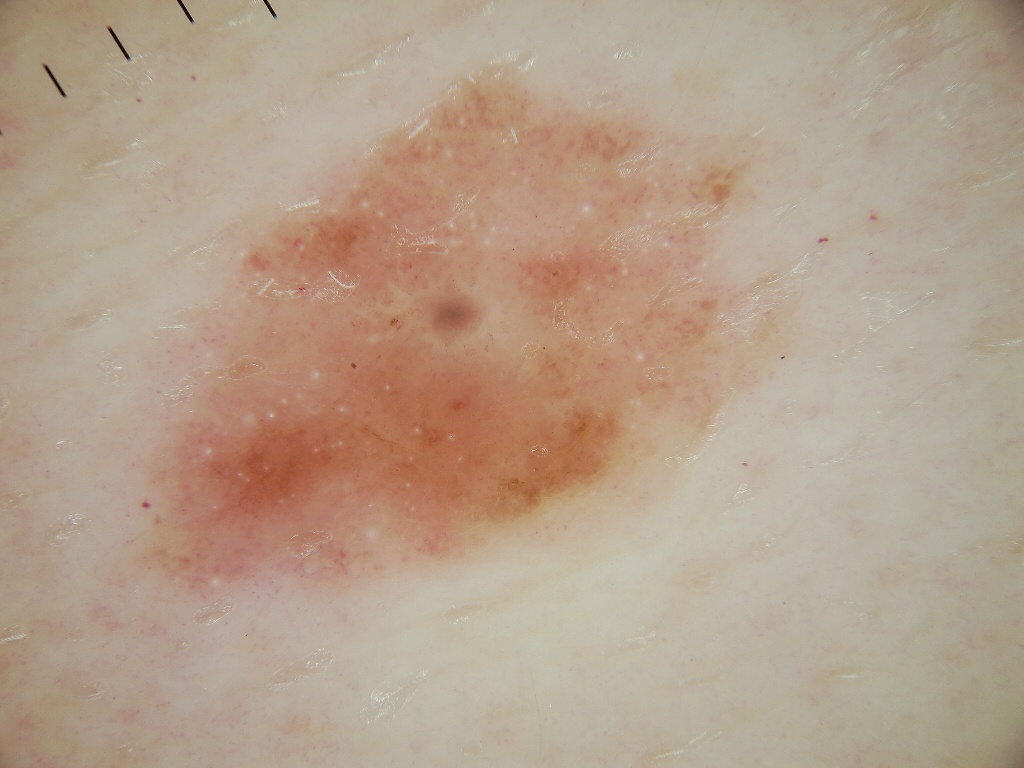| field | value |
|---|---|
| image | dermoscopic image |
| patient | female, roughly 40 years of age |
| extent | moderate |
| bounding box | x1=124 y1=73 x2=746 y2=596 |
| dermoscopic findings | milia-like cysts; absent: globules, streaks, negative network, and pigment network |
| impression | a melanocytic nevus |